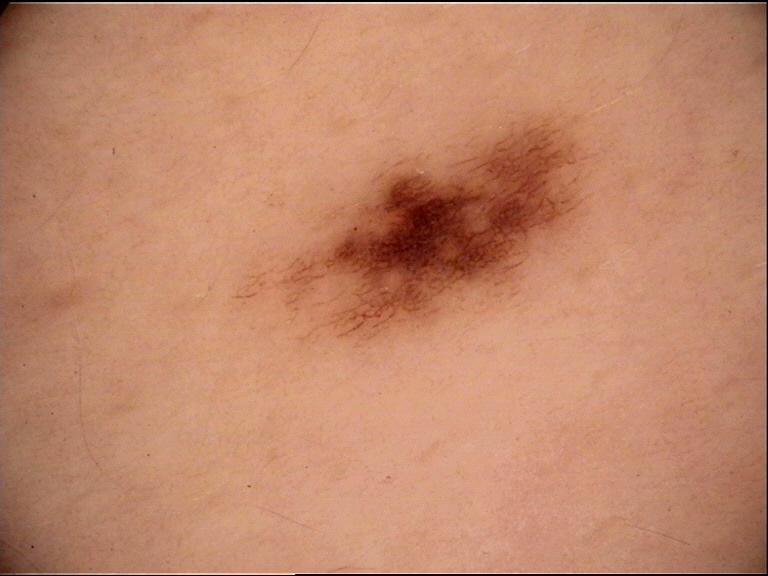A skin lesion imaged with a dermatoscope. The diagnostic label was a benign lesion — a dysplastic junctional nevus.